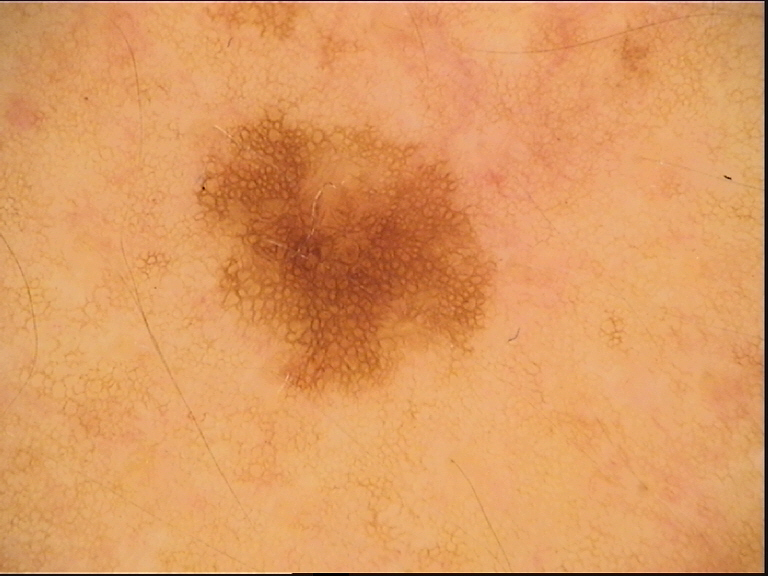assessment = junctional nevus (expert consensus).